This image was taken at an angle, the affected area is the head or neck and front of the torso.
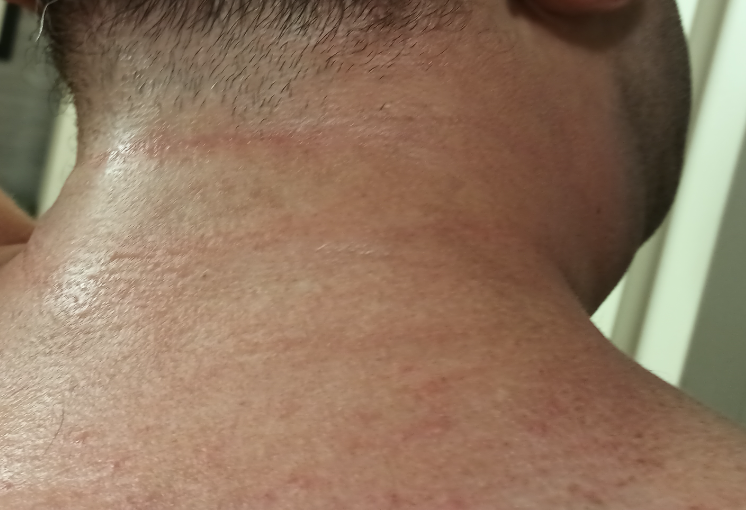Background: Fitzpatrick II. Texture is reported as rough or flaky and raised or bumpy. The contributor notes the condition has been present for less than one week. The contributor notes pain, burning, itching and bothersome appearance. The patient described the issue as a rash. Findings: Single-reviewer assessment: the leading consideration is Irritant Contact Dermatitis; also on the differential is Allergic Contact Dermatitis.